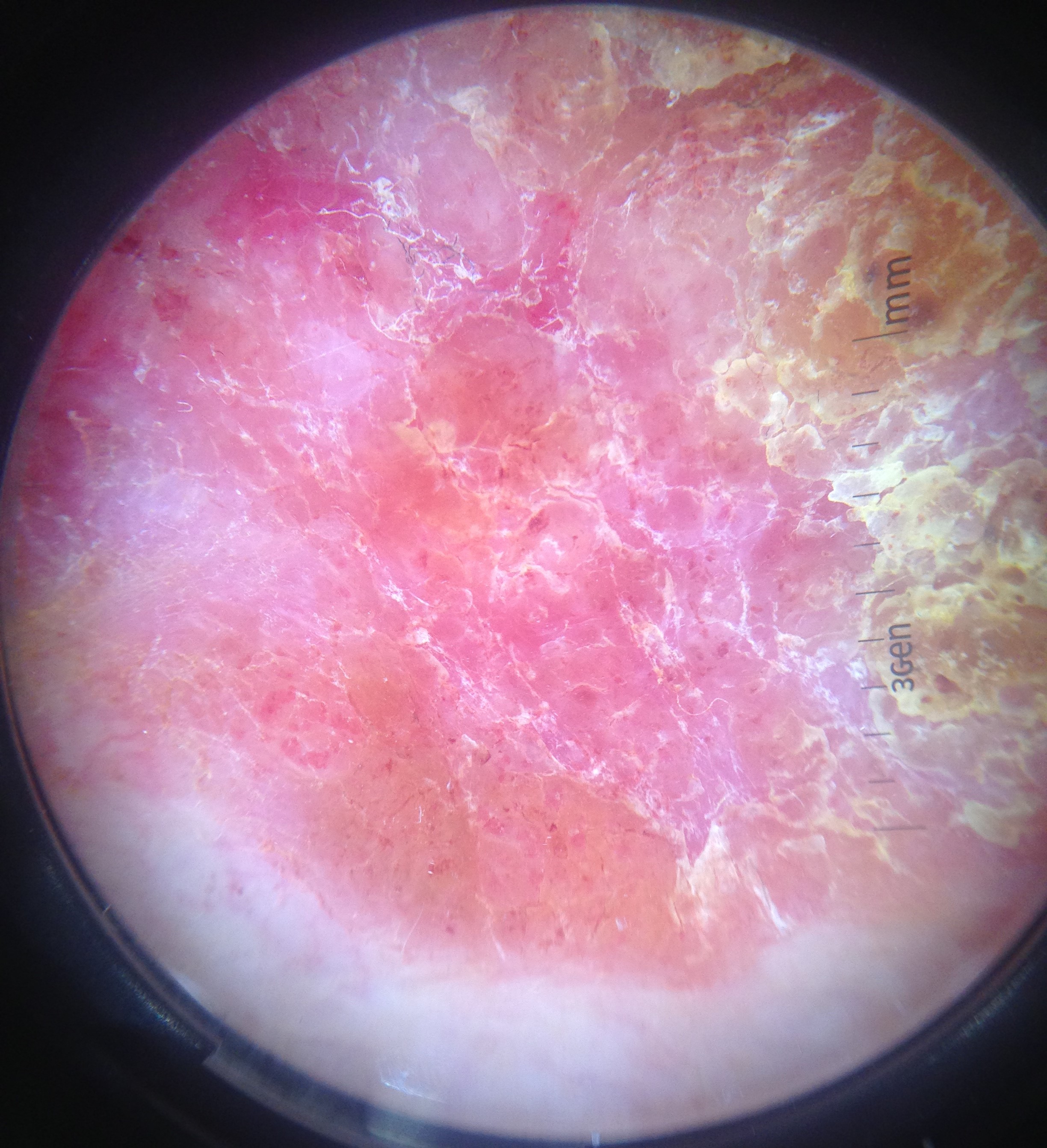Histopathologically confirmed as Bowen's disease.